Close-up view. The affected area is the head or neck, back of the torso and leg:
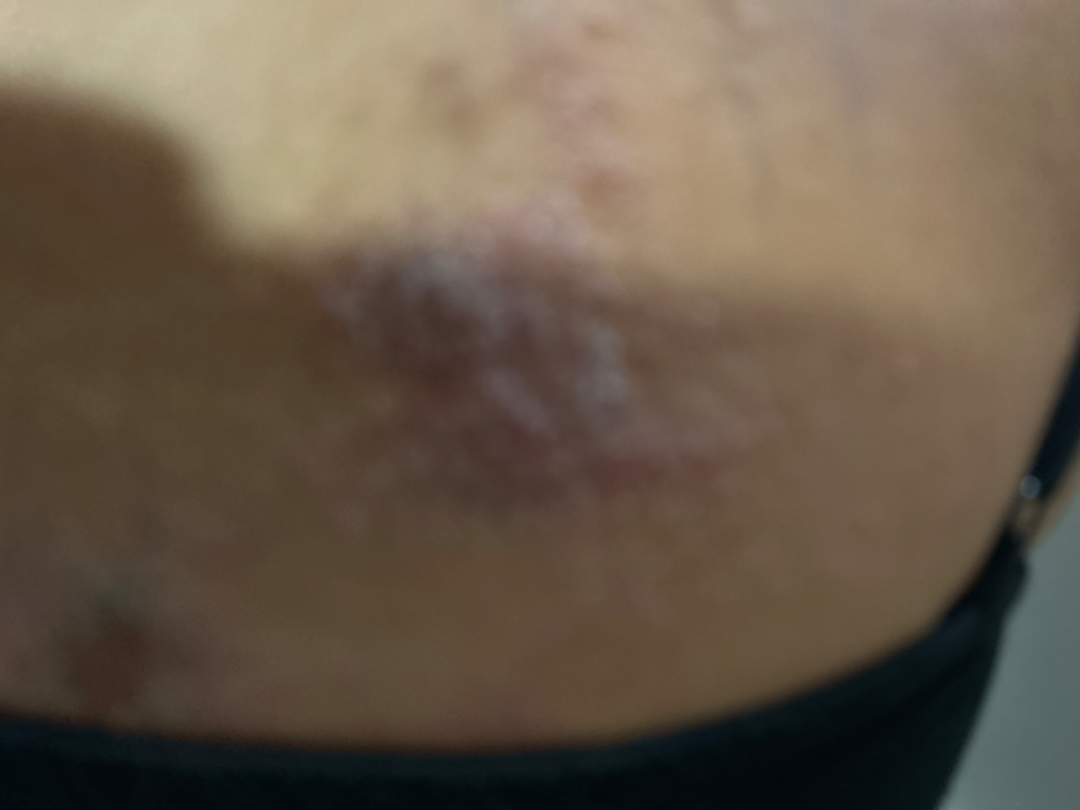The case was difficult to assess from the available photograph.